The lesion is associated with itching, bothersome appearance and enlargement; this image was taken at an angle; the patient reports the lesion is fluid-filled, rough or flaky and raised or bumpy; reported duration is less than one week; the lesion involves the arm.
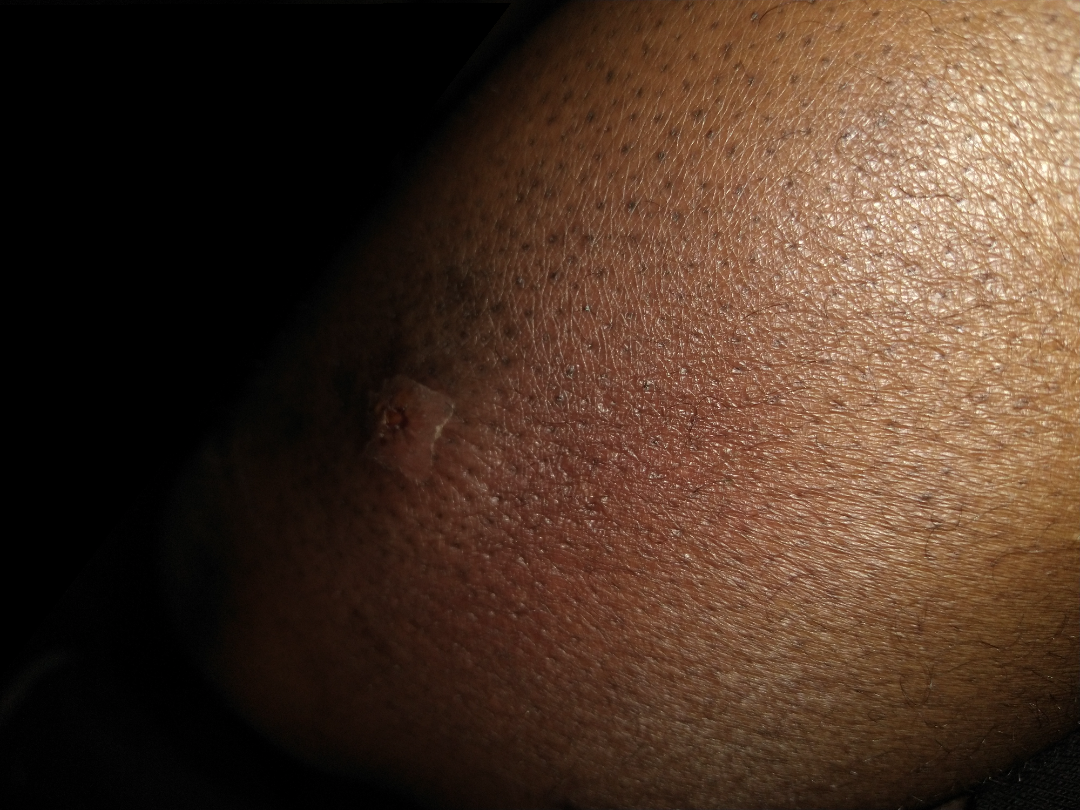The reviewer was unable to grade this case for skin condition.